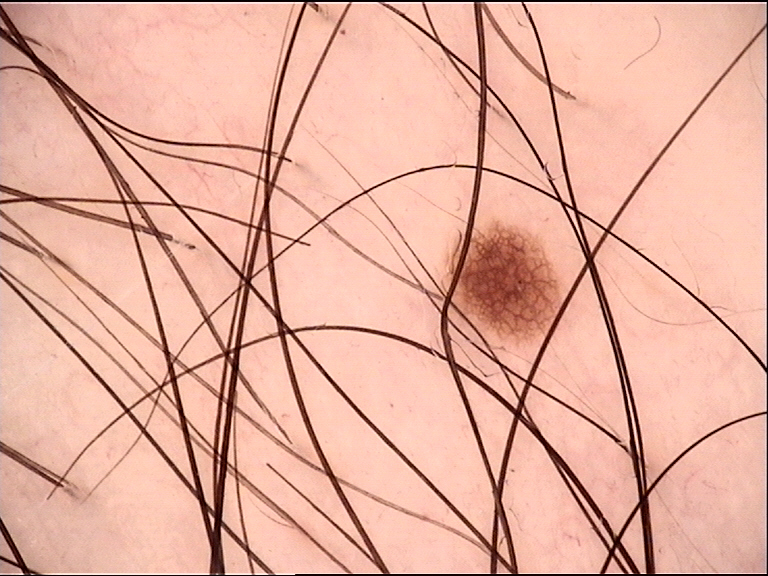imaging: dermoscopy | diagnosis: dysplastic junctional nevus (expert consensus).